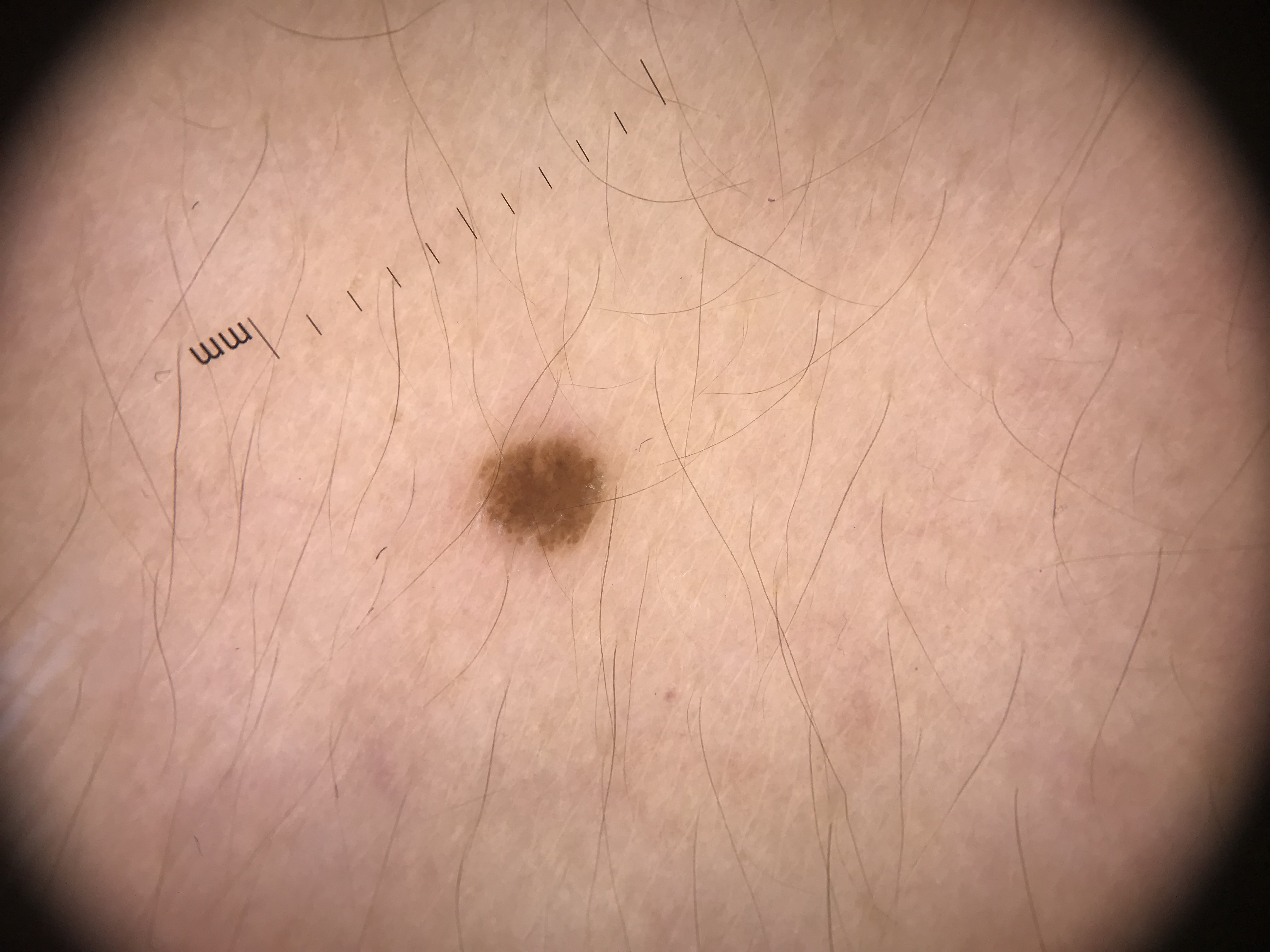A dermoscopic photograph of a skin lesion.
The morphology is that of a banal lesion.
Labeled as a junctional nevus.